The subject is female · the lesion involves the arm, leg and back of the hand · an image taken at a distance.
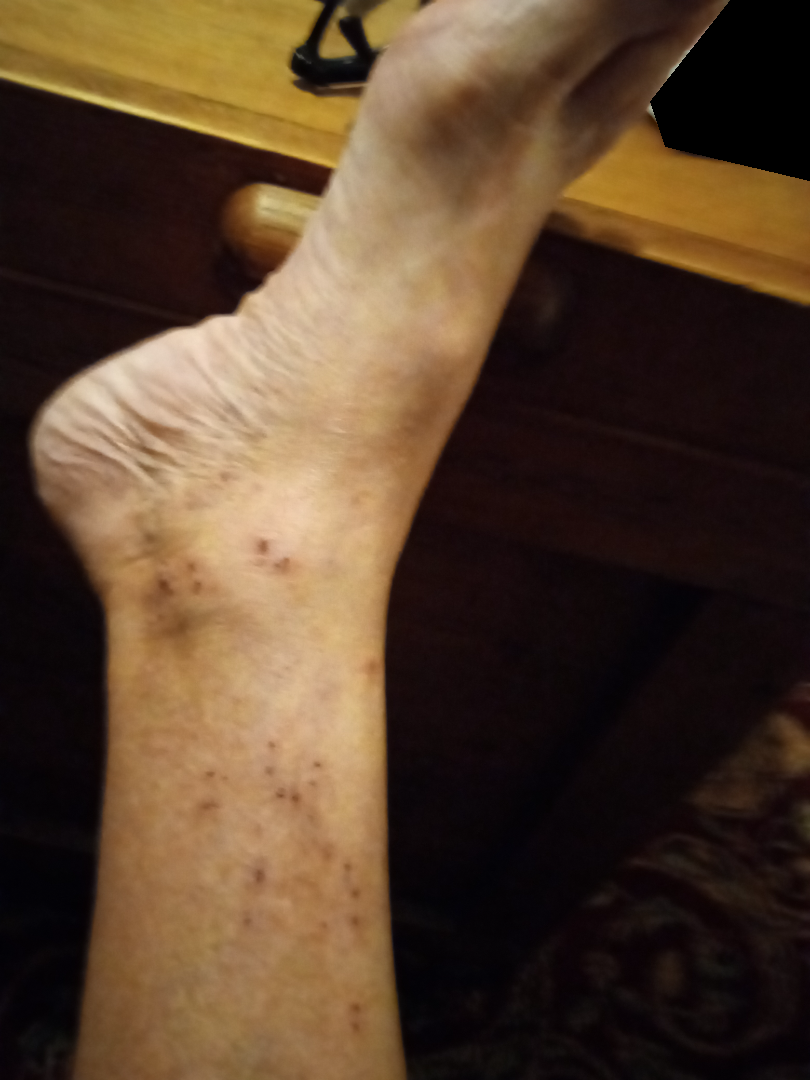lesion symptoms — itching; symptom duration — more than one year; self-categorized as — a rash; diagnostic considerations — most consistent with Eczema.